A dermoscopy image of a single skin lesion.
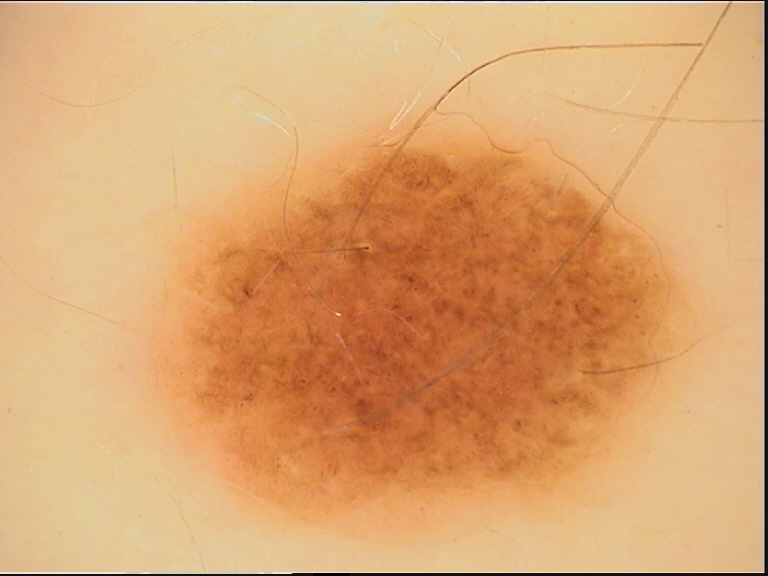classification: banal; diagnosis: compound nevus (expert consensus).